A dermoscopic close-up of a skin lesion.
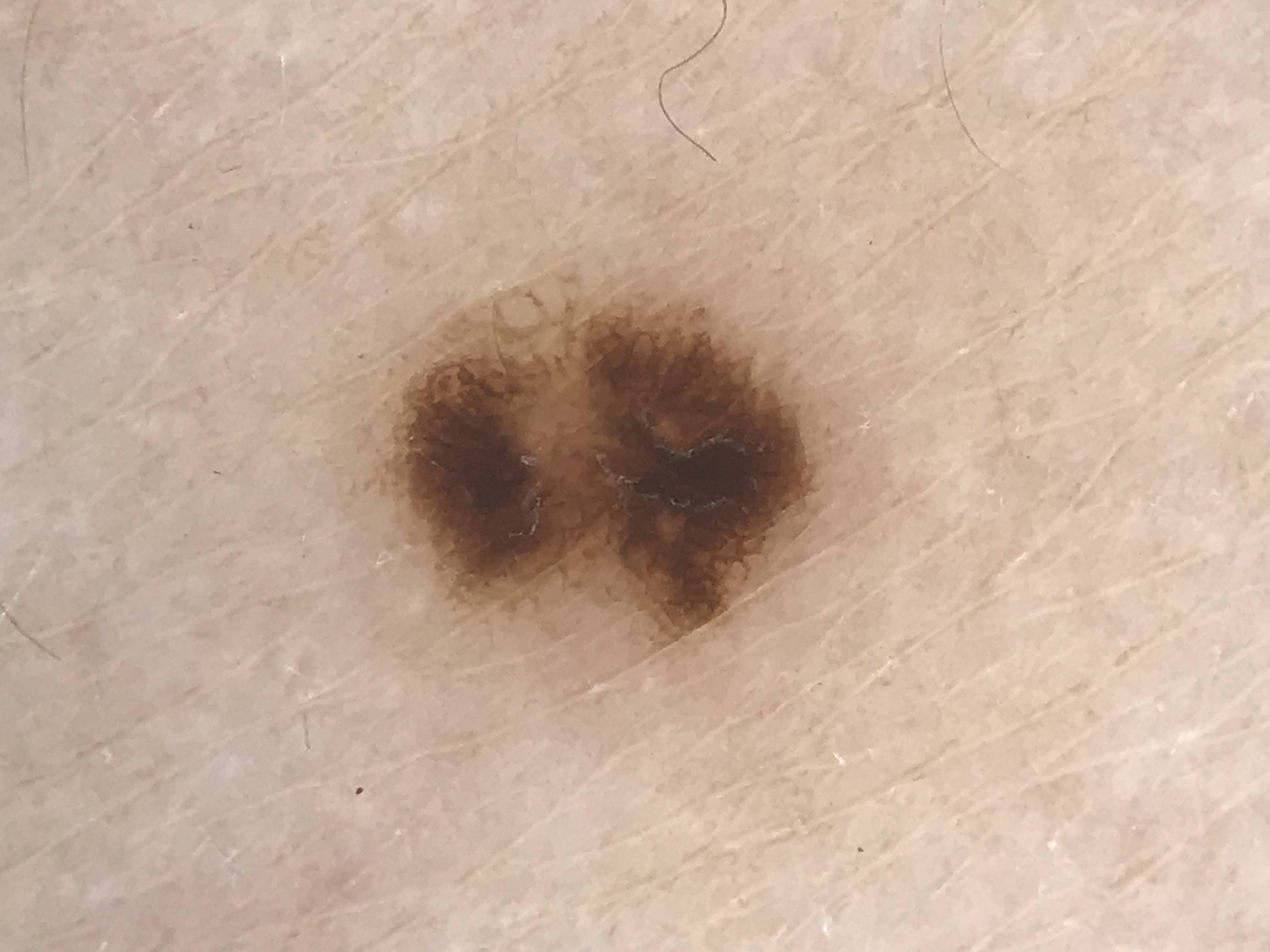diagnosis — dysplastic junctional nevus (expert consensus)